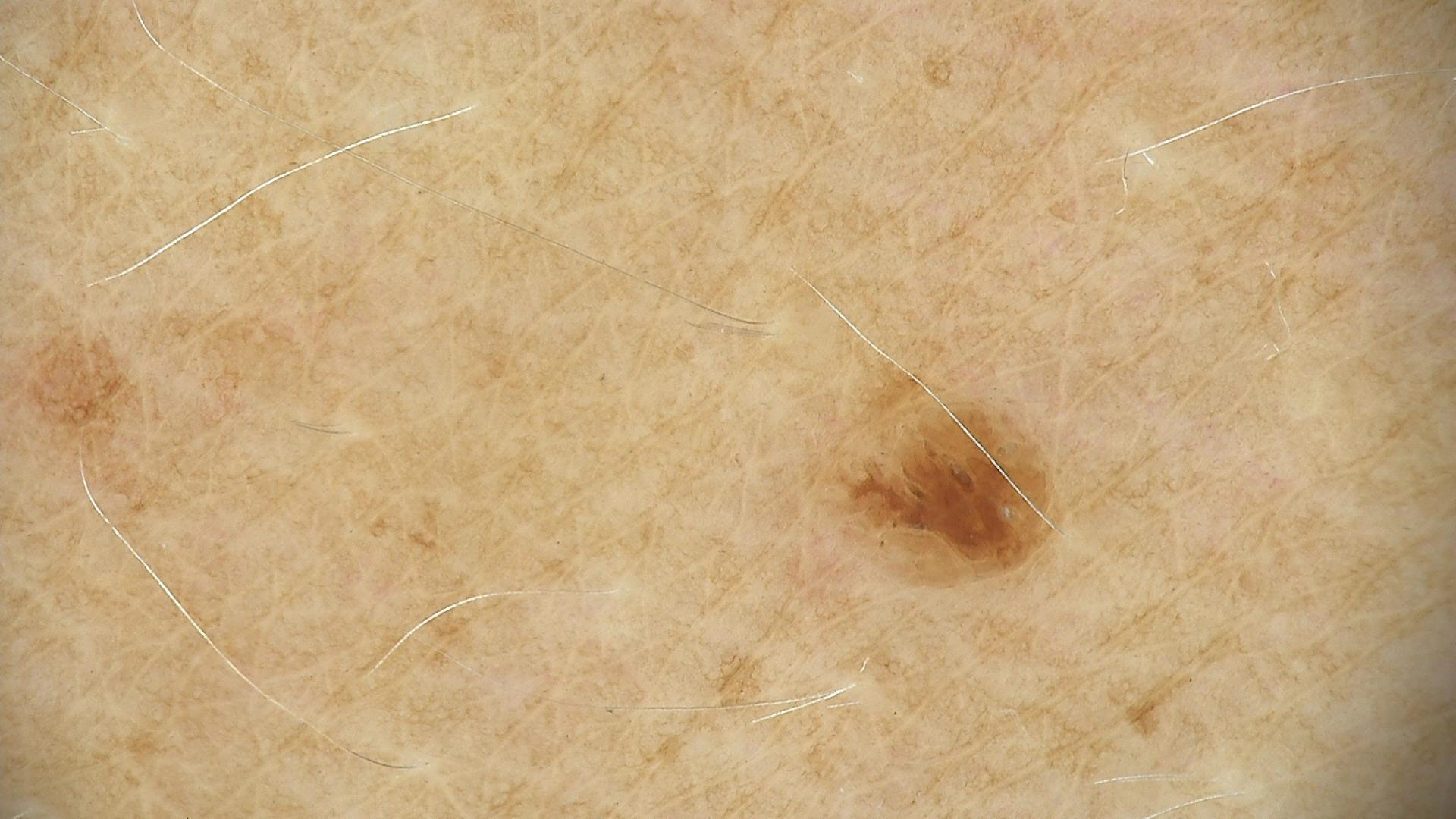Impression: Labeled as a seborrheic keratosis.